A dermoscopic photograph of a skin lesion.
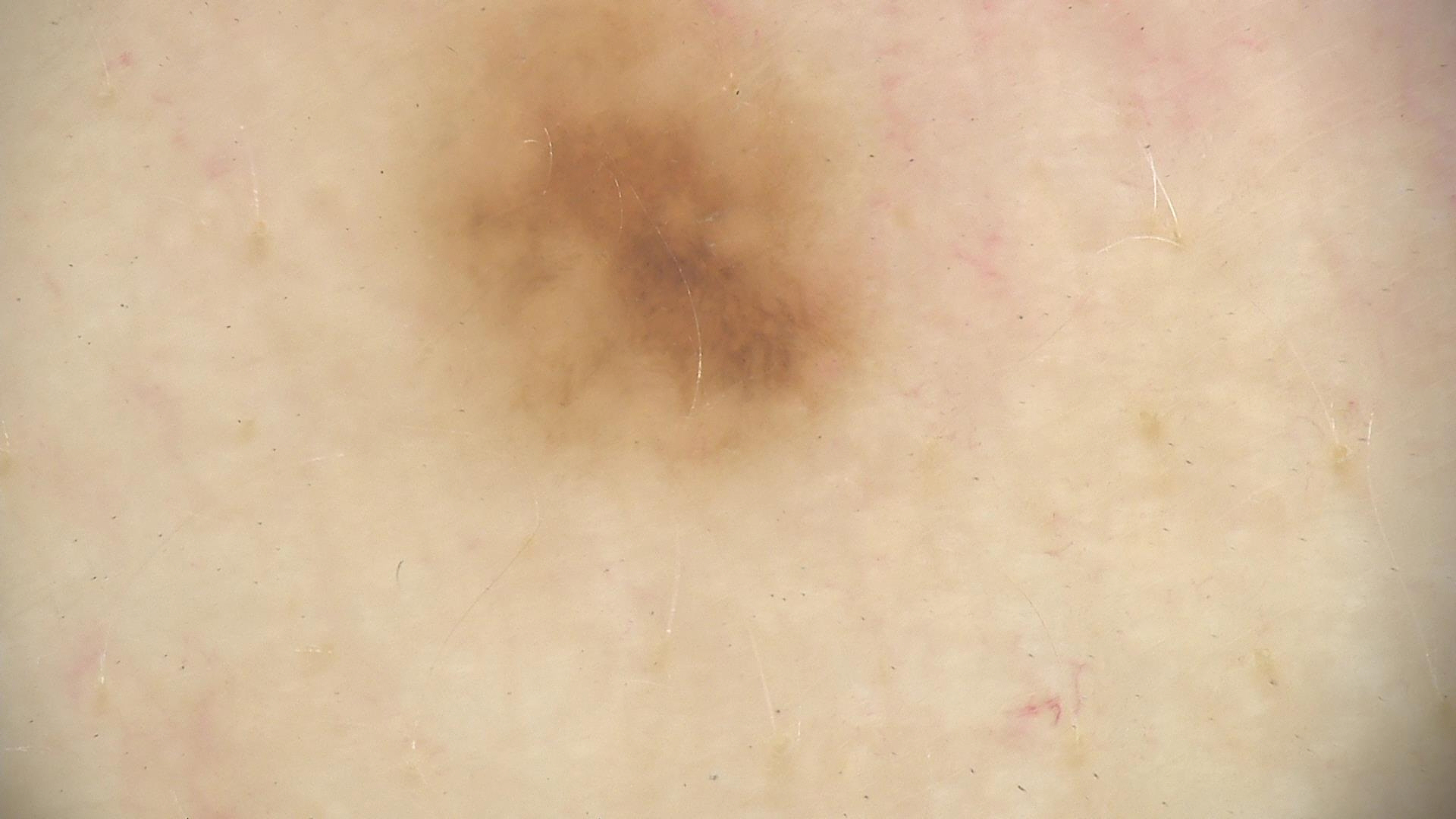The diagnostic label was a dysplastic junctional nevus.